A clinical close-up photograph of a skin lesion; a patient in their late 60s — 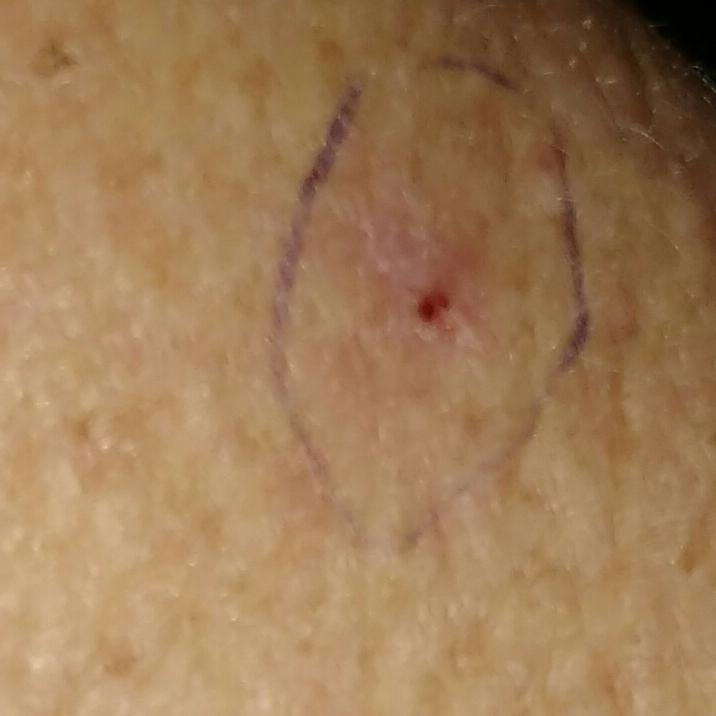Located on an arm. By the patient's account, the lesion has bled and itches. The consensus clinical diagnosis was a premalignant lesion — an actinic keratosis.